A close-up photograph — 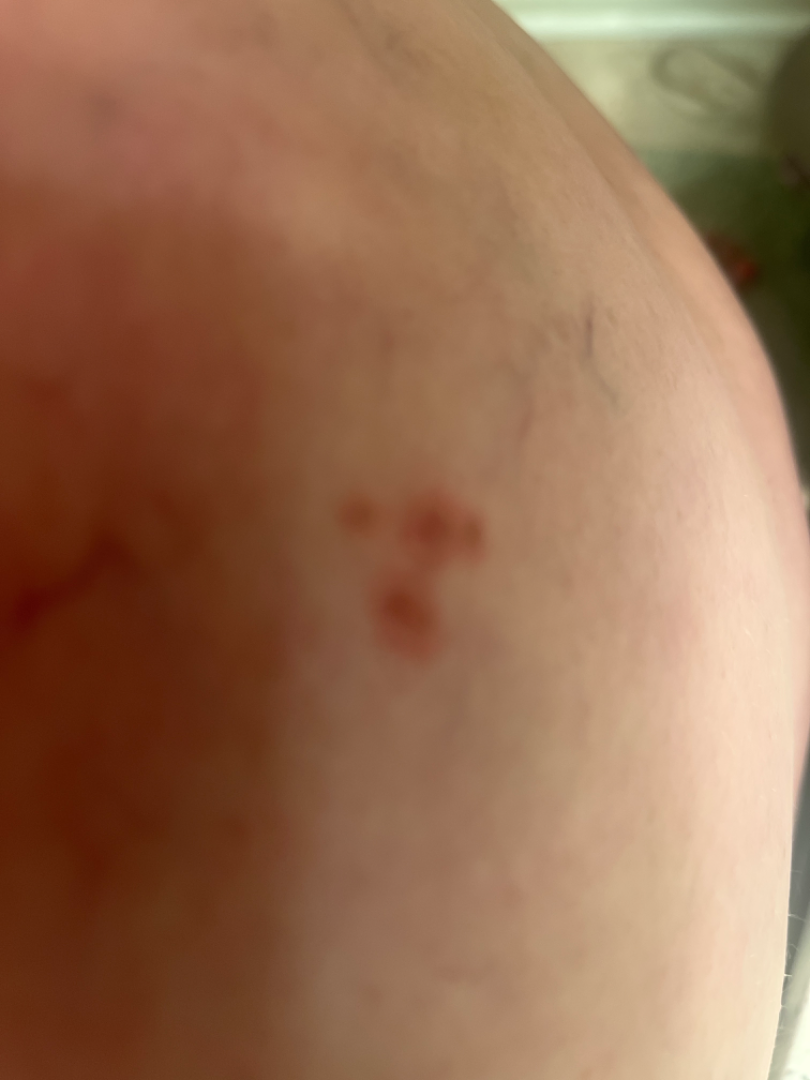Case summary:
- dermatologist impression — single-reviewer assessment: the leading consideration is Insect Bite; also on the differential is Impetigo; also raised was Eczema